The chart records prior malignancy (patient or family) and prior skin cancer (patient or family) · a clinical photo of a skin lesion taken with a smartphone · a female subject in their early 80s — 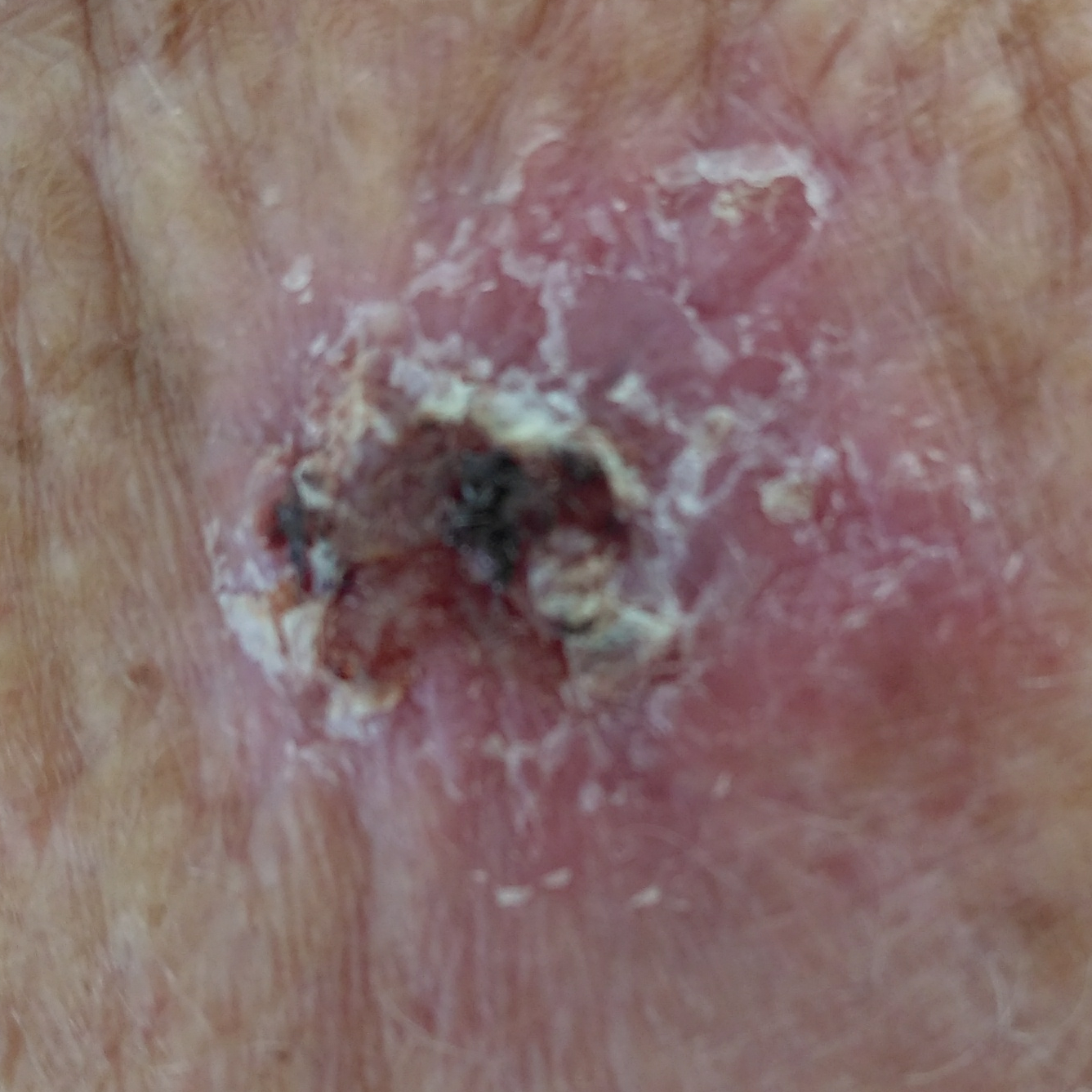| feature | finding |
|---|---|
| location | a forearm |
| diameter | 21 × 20 mm |
| patient-reported symptoms | itching, bleeding, pain |
| diagnosis | basal cell carcinoma (biopsy-proven) |